Symptoms reported: itching, the photograph was taken at an angle, the affected area is the back of the hand, skin tone: Fitzpatrick skin type II; lay reviewers estimated MST 2 or 3 (two reviewer pools).
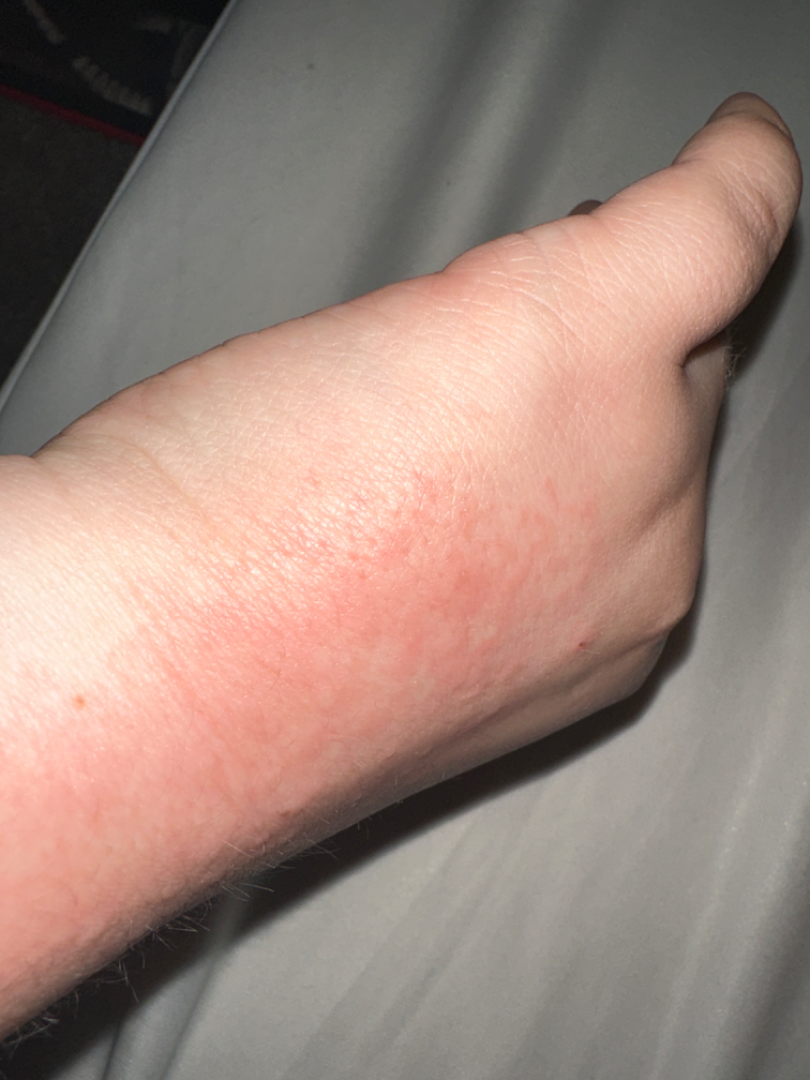No differential diagnosis could be assigned on photographic review.